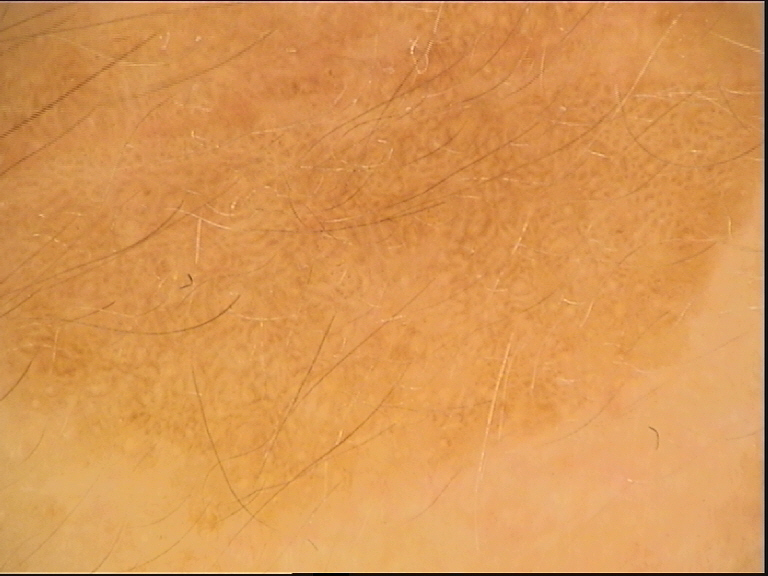* imaging · dermoscopy
* diagnosis · seborrheic keratosis (expert consensus)